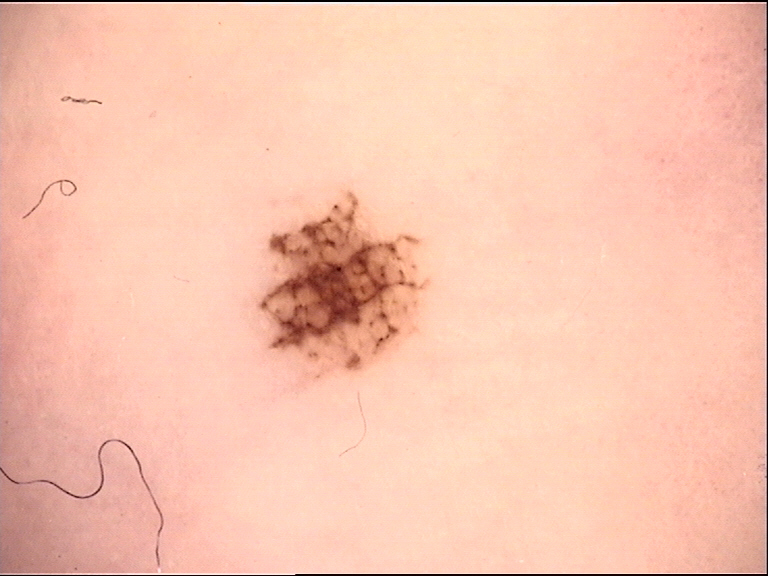Case:
A dermatoscopic image of a skin lesion.
Conclusion:
The diagnosis was an acral dysplastic junctional nevus.